Few moles overall by the patient's own estimate; a male subject 66 years old; by self-report, a prior organ transplant, no immunosuppression, and no personal history of cancer; the patient says their skin reddens with sun exposure; referred with a clinical suspicion of basal cell carcinoma.
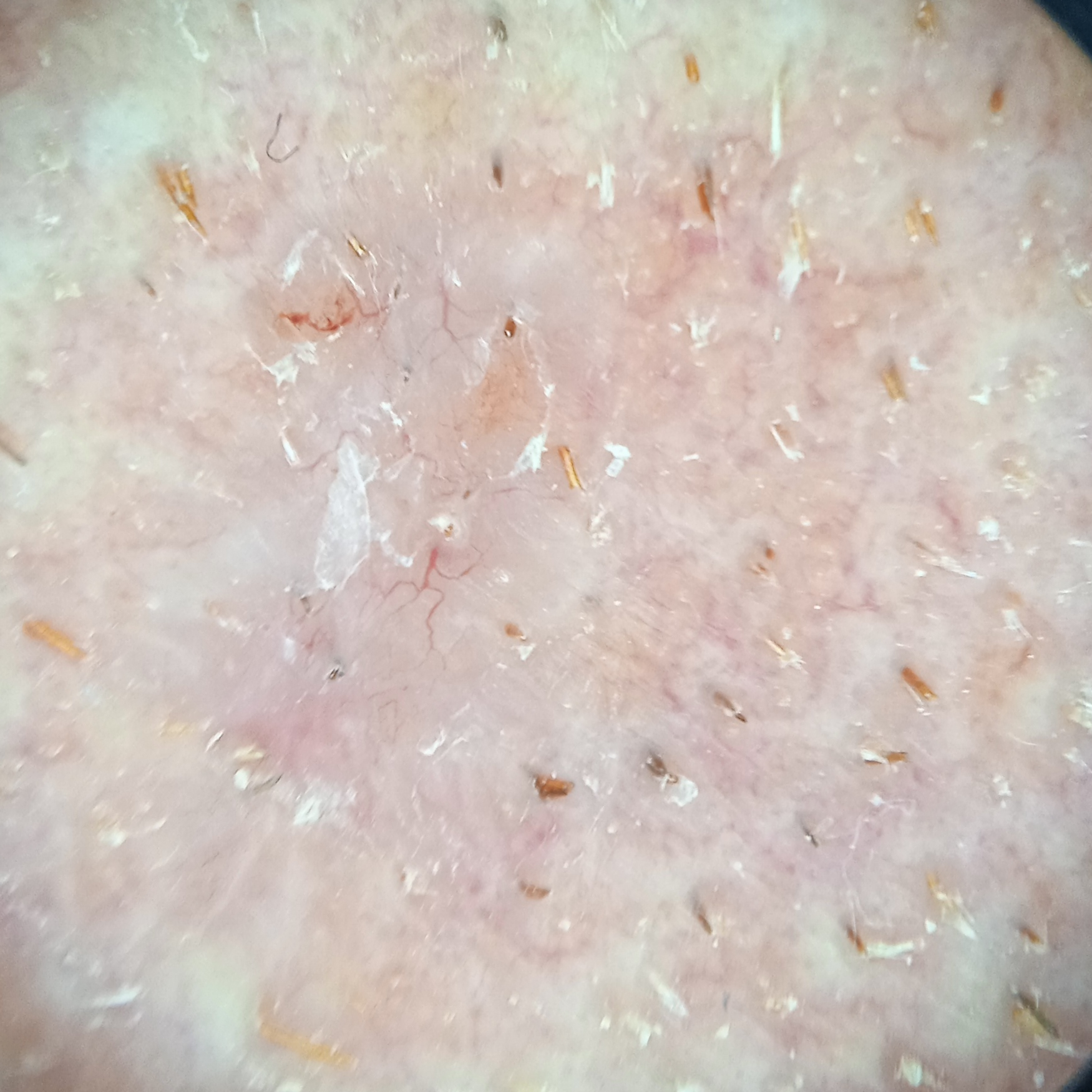body site = the face
lesion size = 7.5 mm
diagnosis = basal cell carcinoma (biopsy-proven)